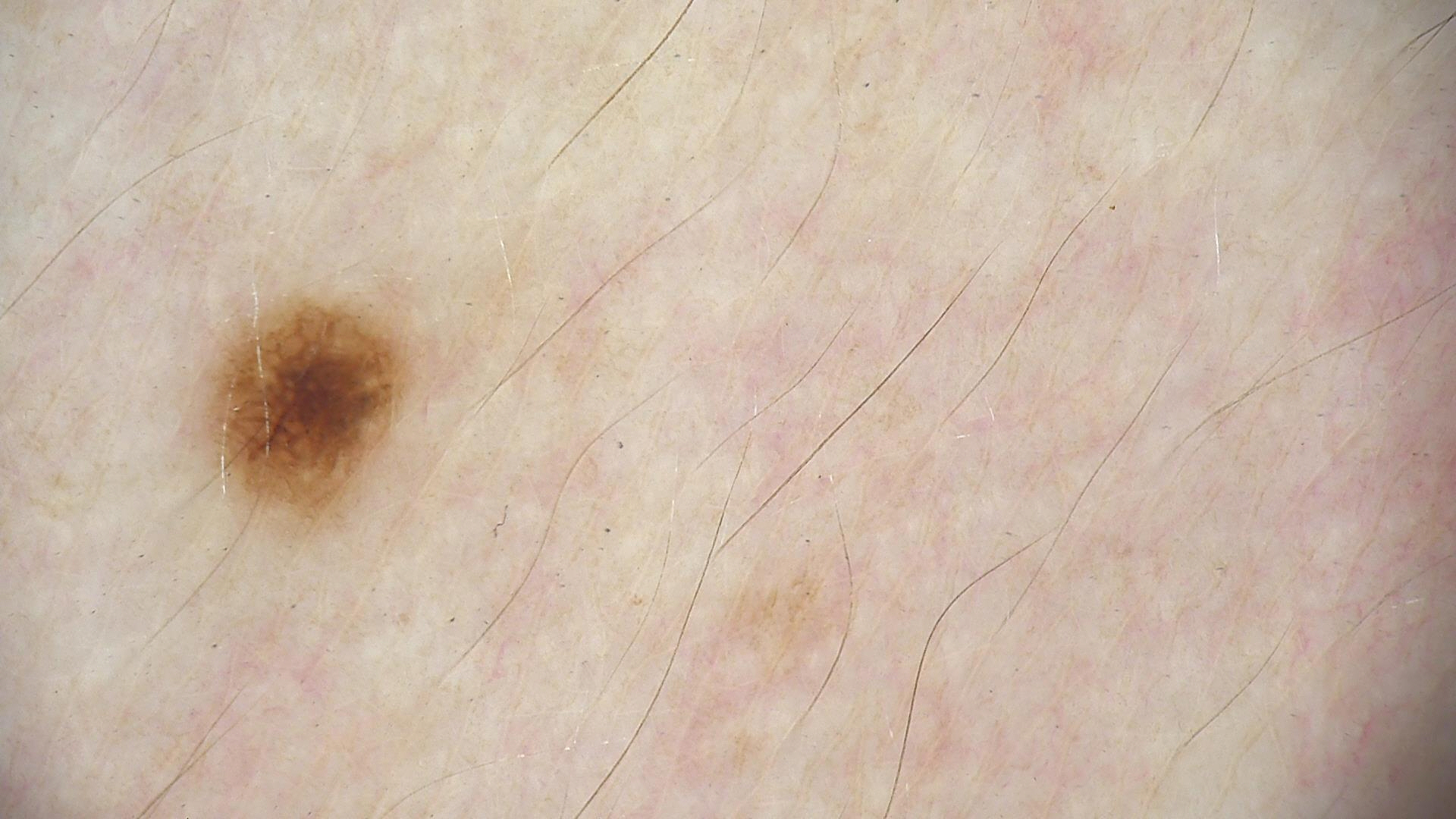Consistent with a junctional nevus.